A dermatoscopic image of a skin lesion: 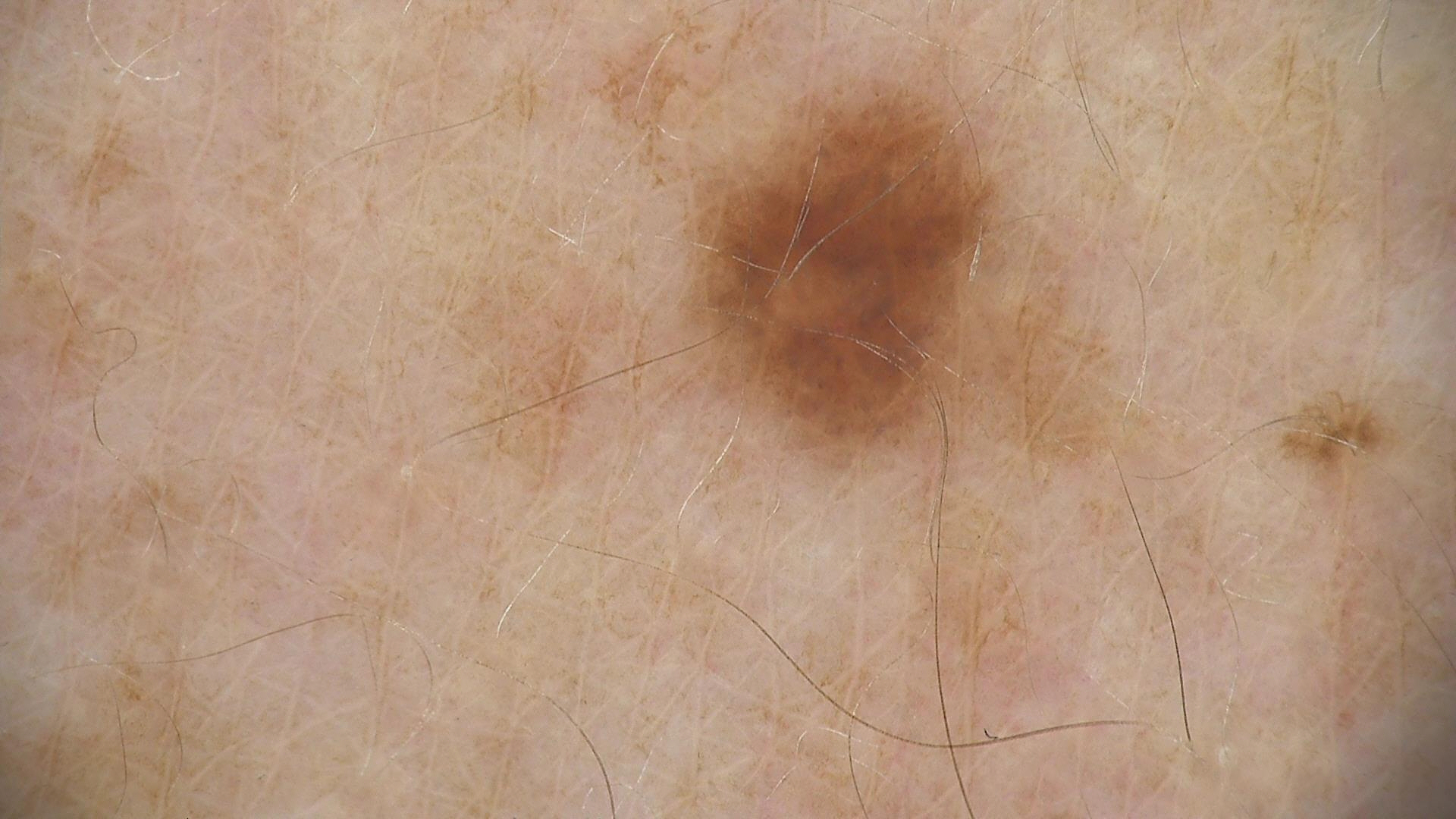Impression:
Labeled as a dysplastic junctional nevus.